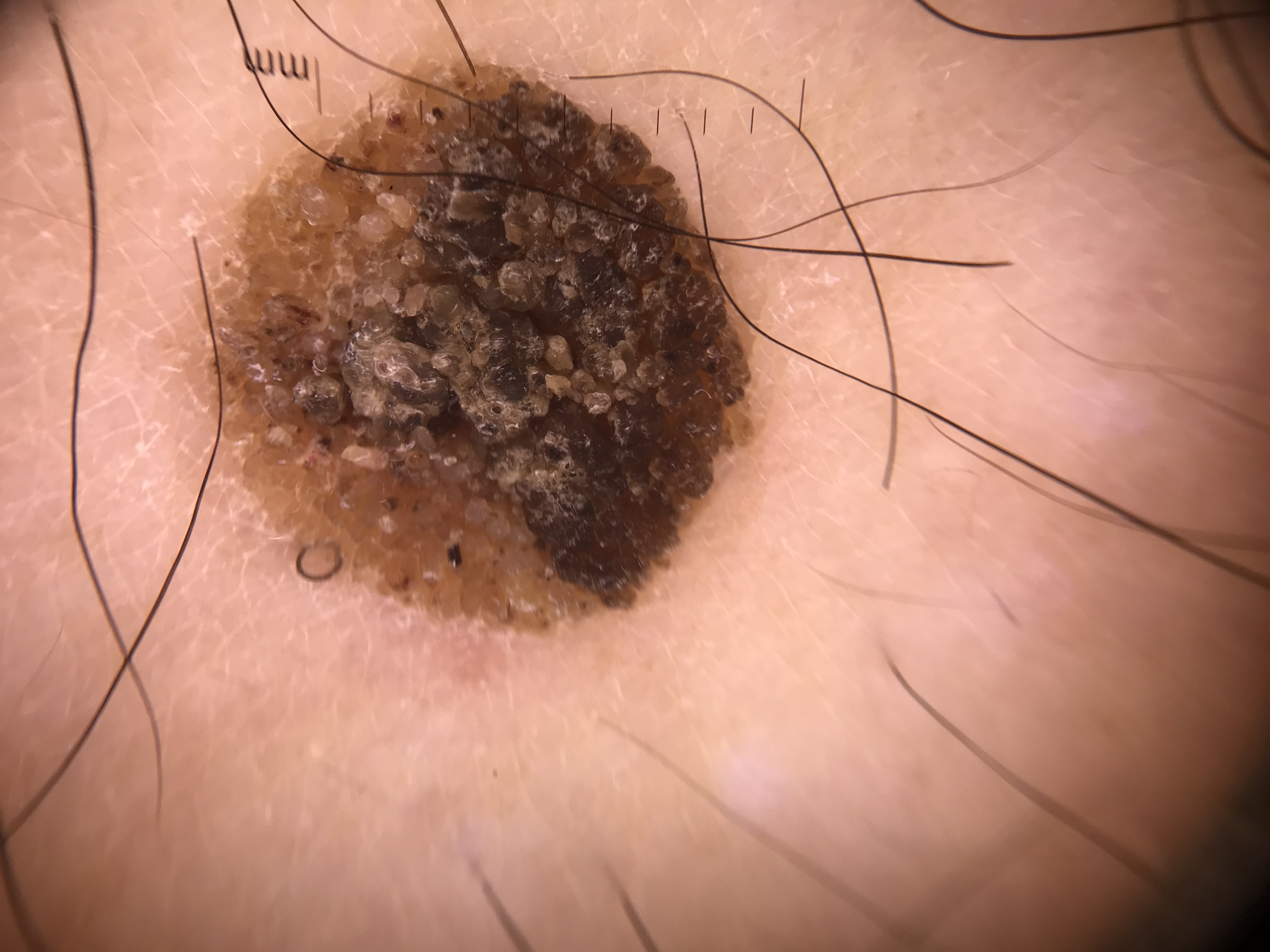Consistent with a keratinocytic lesion — a seborrheic keratosis.